The photograph was taken at a distance · the affected area is the arm, head or neck, front of the torso, leg, back of the hand and palm: 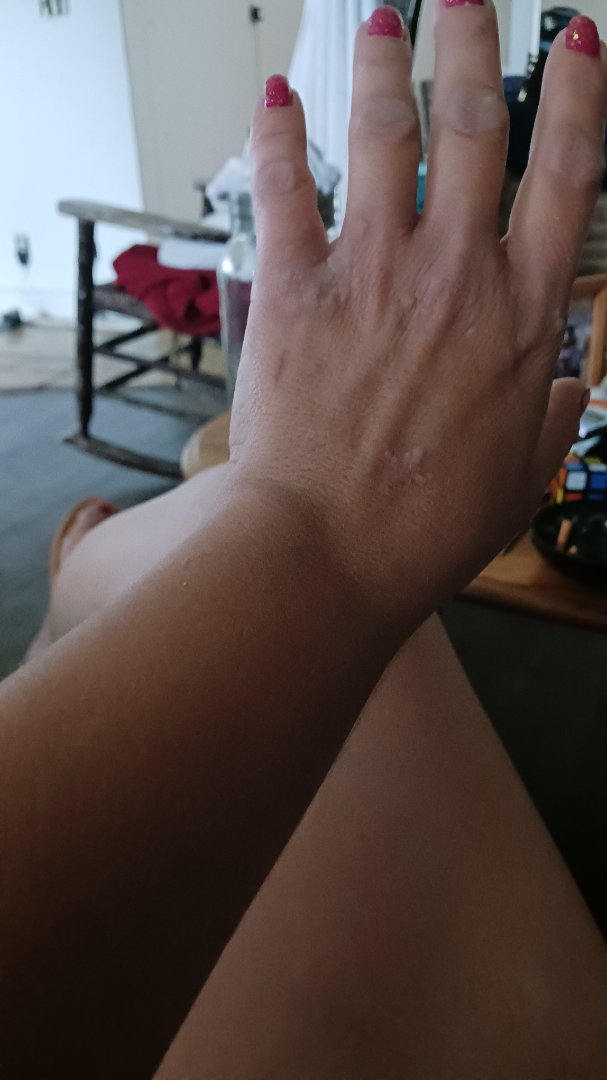Notes:
• dermatologist impression · most consistent with Verruca vulgaris; an alternative is Lichen planus/lichenoid eruption